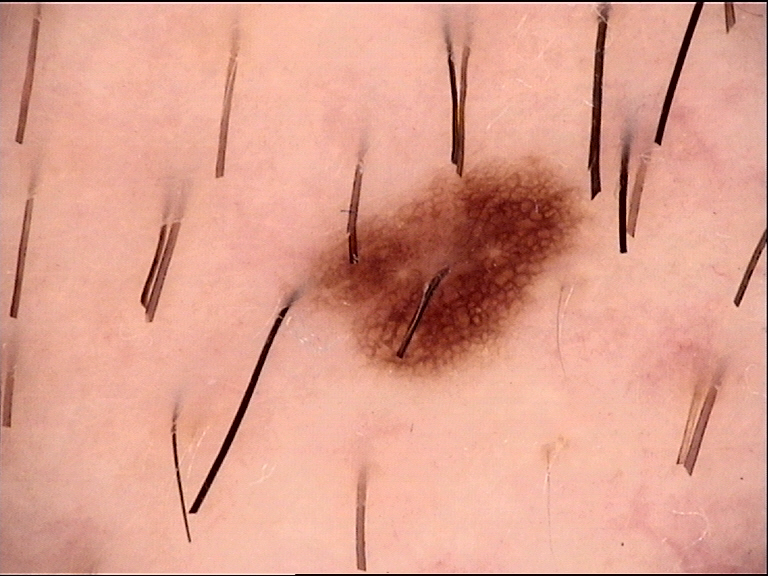Conclusion: The diagnosis was a dysplastic junctional nevus.